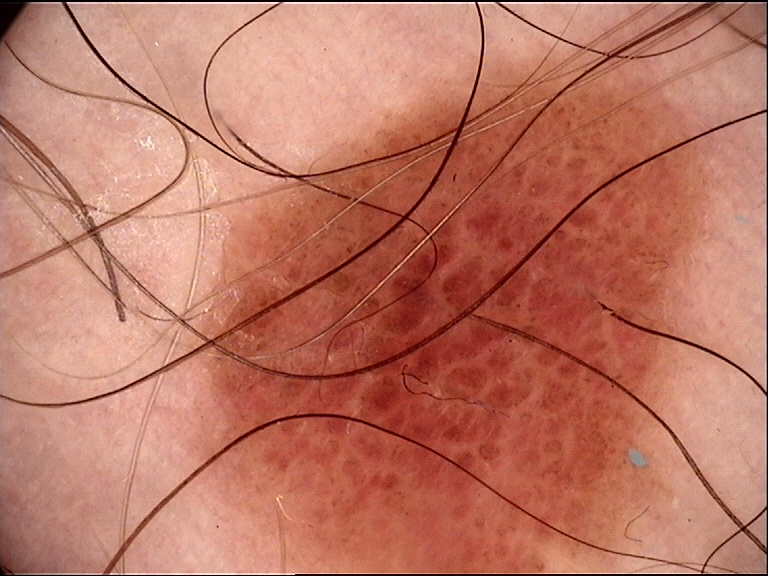Classified as a banal lesion — a compound nevus.